A dermoscopy image of a single skin lesion.
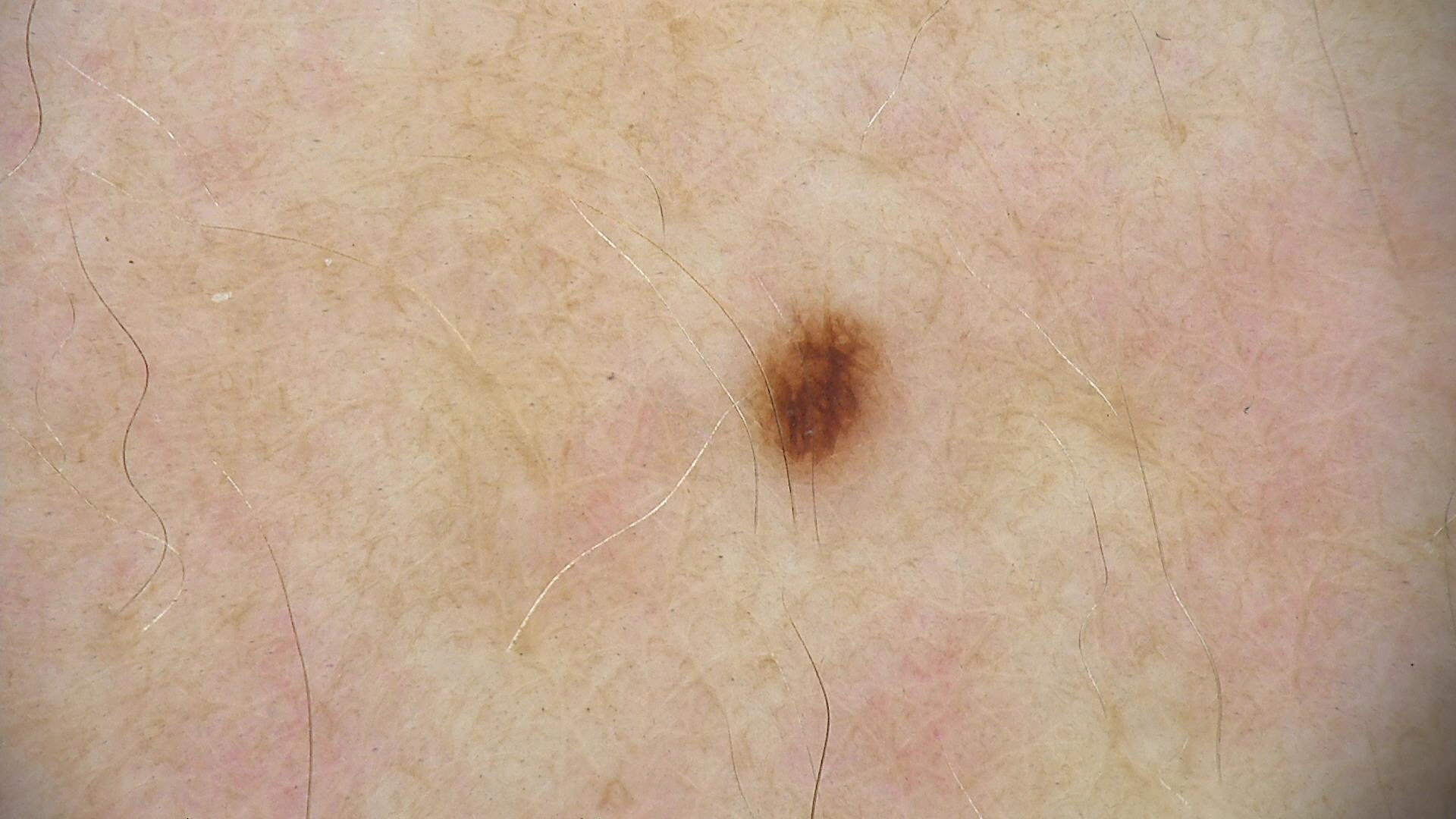label = dysplastic junctional nevus (expert consensus).